The leg is involved; female subject, age 18–29; the patient indicates the lesion is raised or bumpy; reported duration is about one day; reported lesion symptoms include itching; the patient reported no systemic symptoms; close-up view — 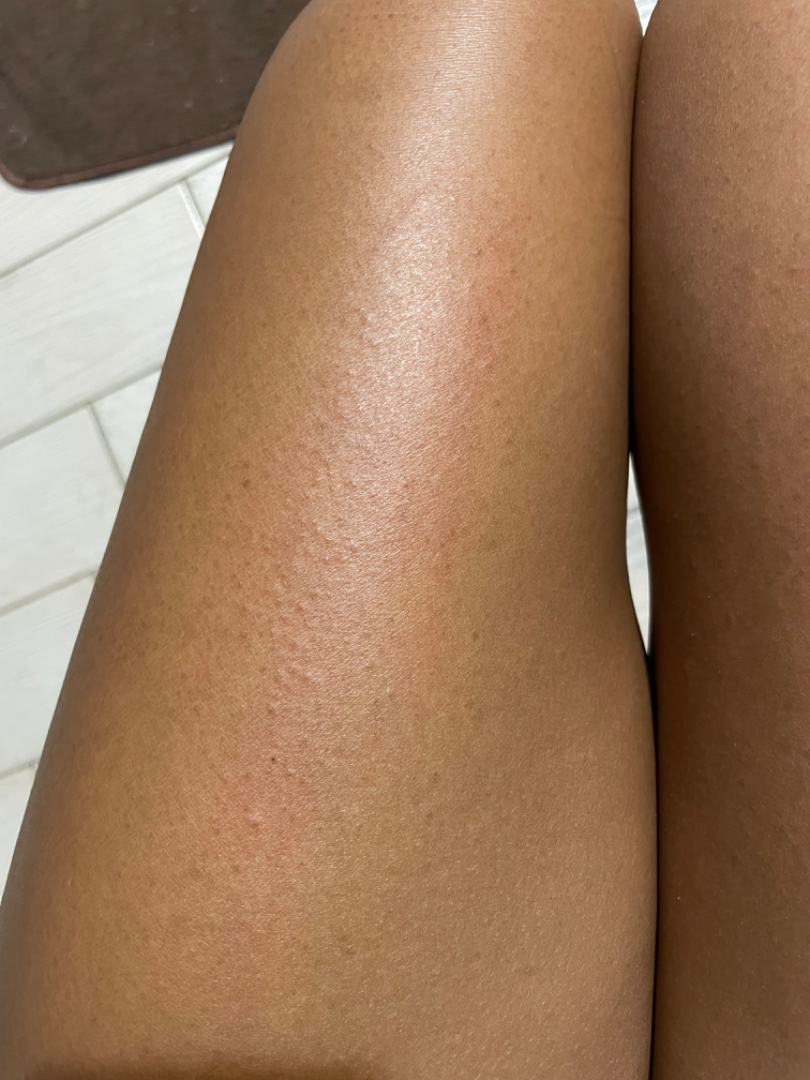Findings:
* differential · the leading consideration is Keratosis pilaris; also raised was Eczema